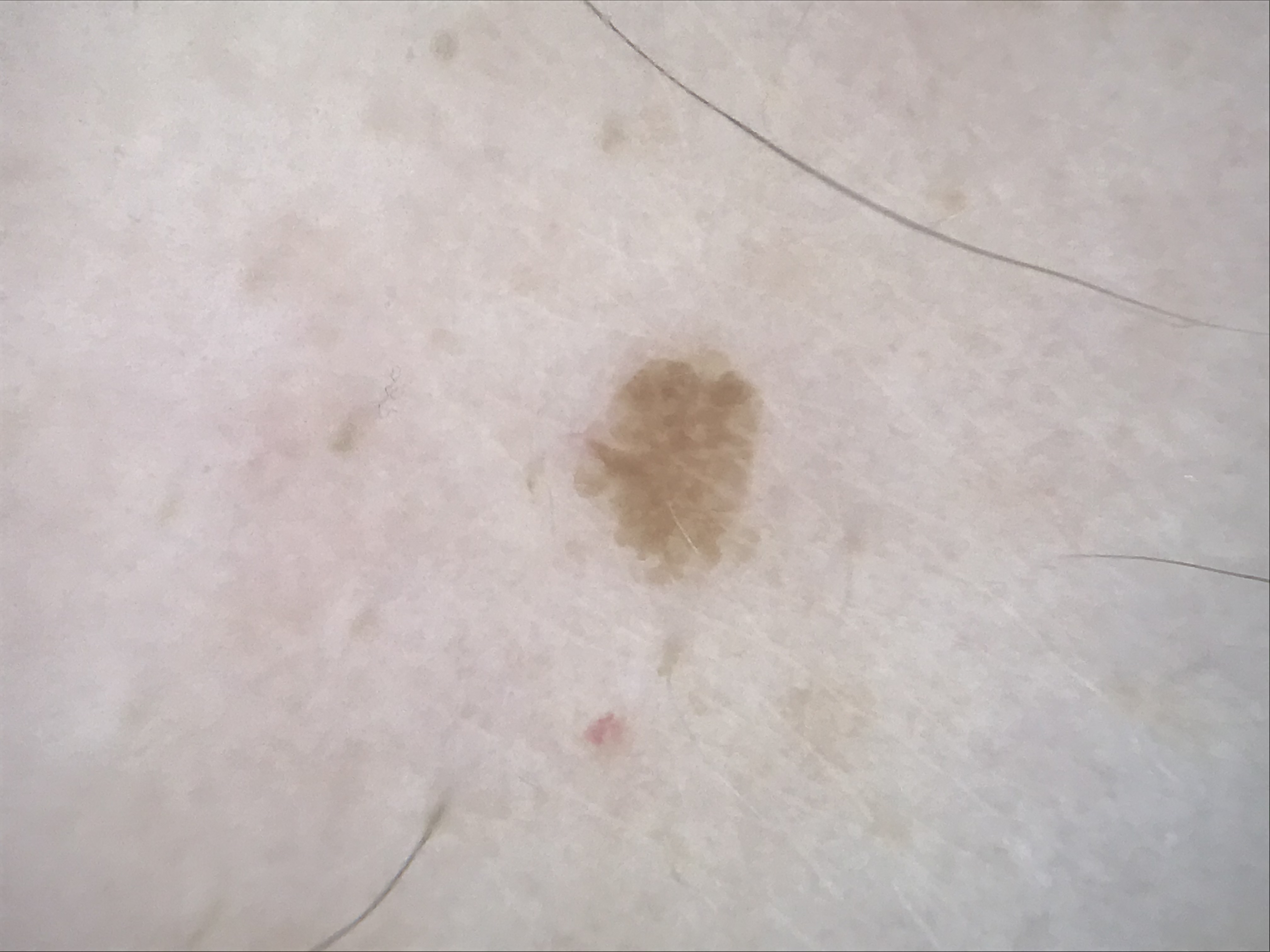image type = dermatoscopy
category = keratinocytic
diagnostic label = seborrheic keratosis (expert consensus)